By history, prior skin cancer (patient or family), prior malignancy (patient or family), and pesticide exposure; a clinical photograph showing a skin lesion; the patient is FST II; a male patient in their late 30s: 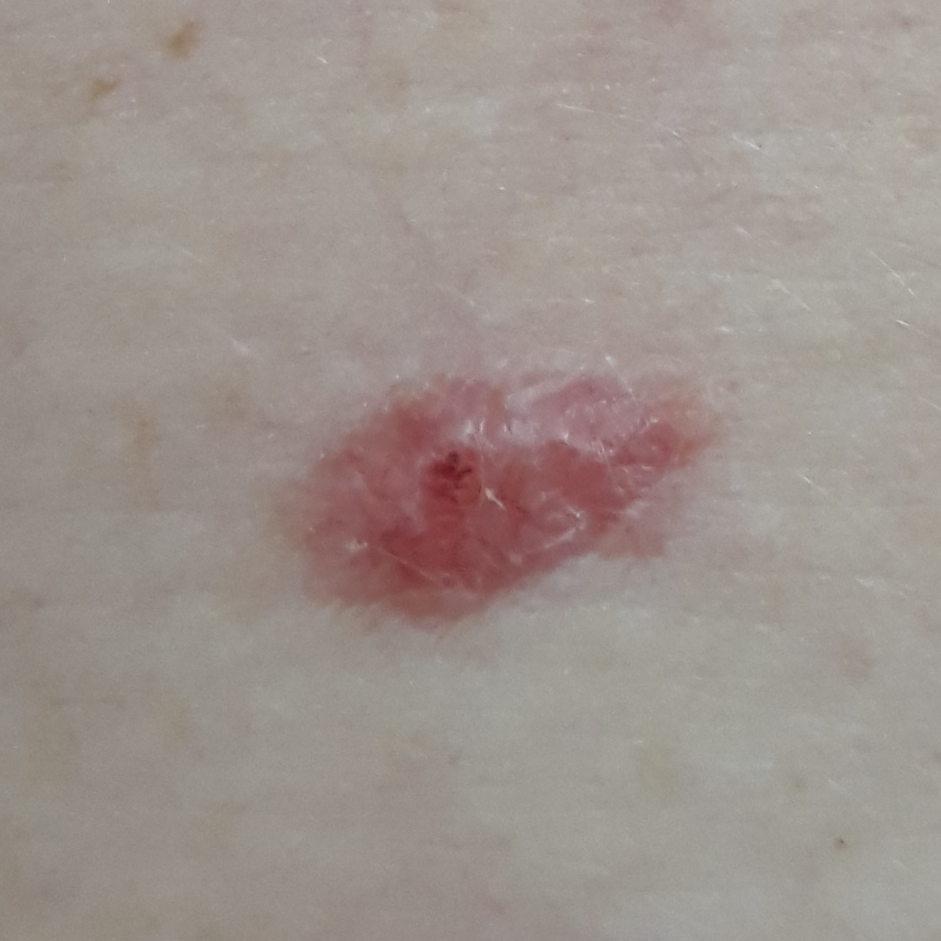Case:
– location — the abdomen
– diameter — 10x5 mm
– reported symptoms — itching, elevation
– pathology — basal cell carcinoma (biopsy-proven)